This is a close-up image. The subject is 18–29, female. The affected area is the leg.
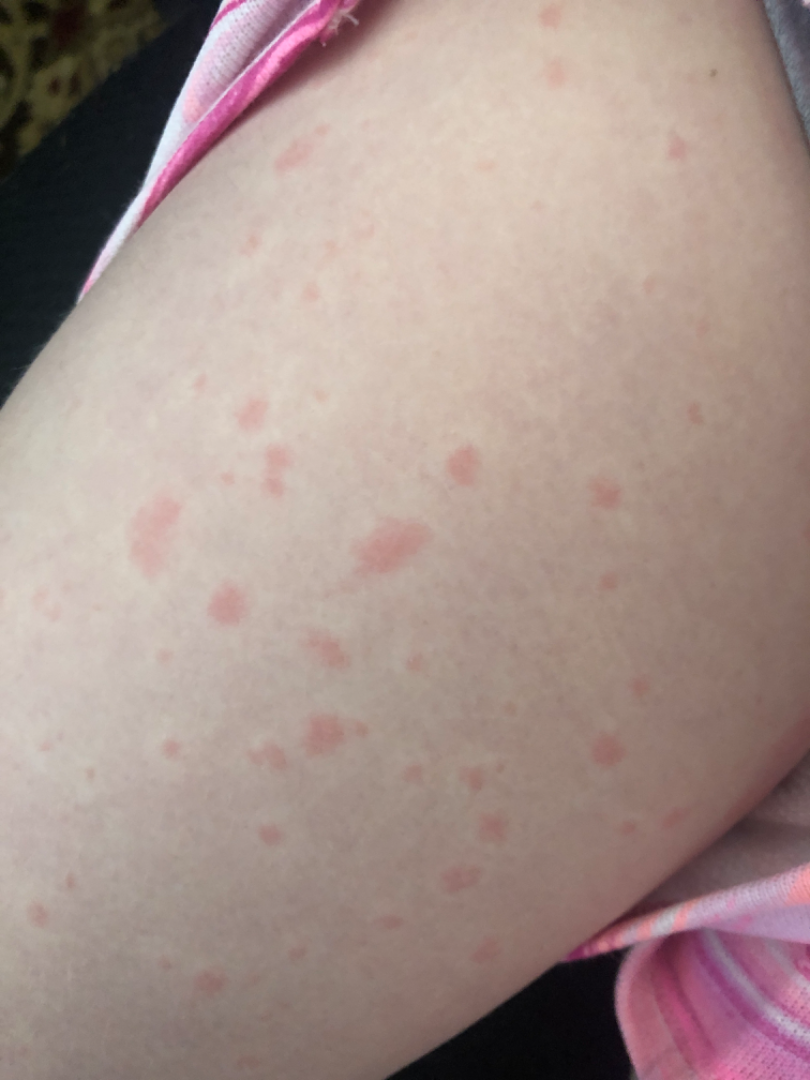The condition has been present for about one day.
The lesion is described as flat.
The patient reported no relevant symptoms from the lesion.
Skin tone: Fitzpatrick II; non-clinician graders estimated Monk Skin Tone 2.
Reviewed remotely by one dermatologist: most consistent with Urticaria.